A dermoscopic photograph of a skin lesion.
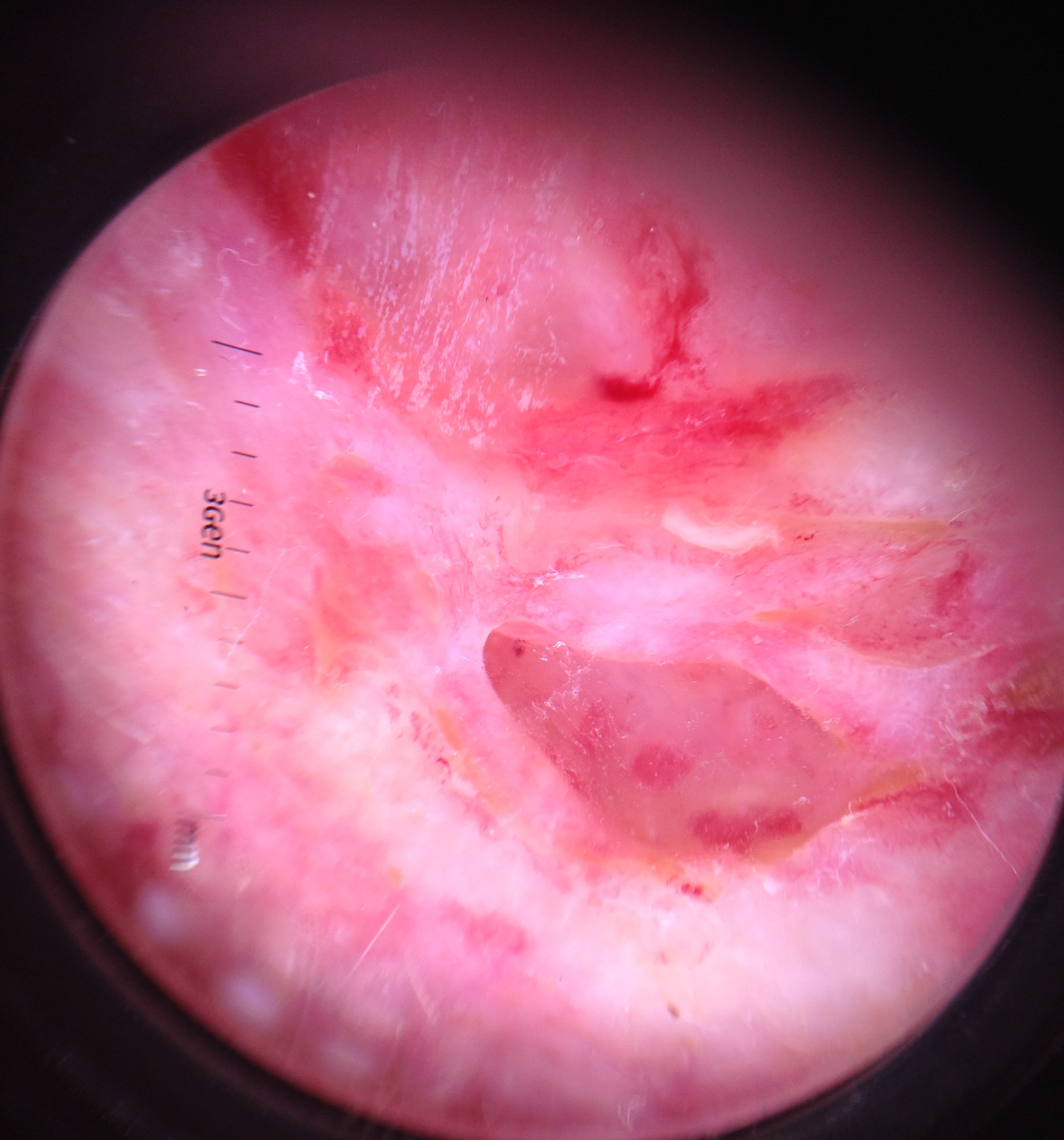The morphology is that of a keratinocytic lesion. The biopsy diagnosis was a squamous cell carcinoma.